The photo was captured at a distance: 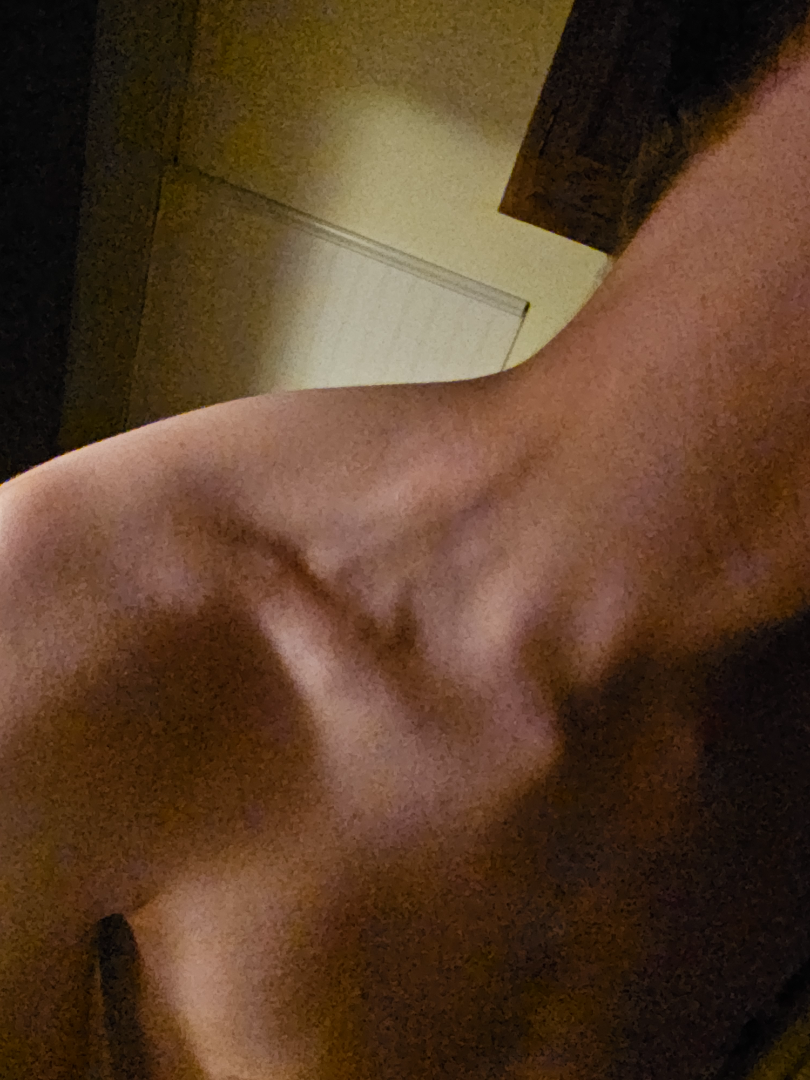Impression: On remote review of the image, Pityriasis rosea (possible); Tinea Versicolor (possible); Seborrheic Dermatitis (possible).